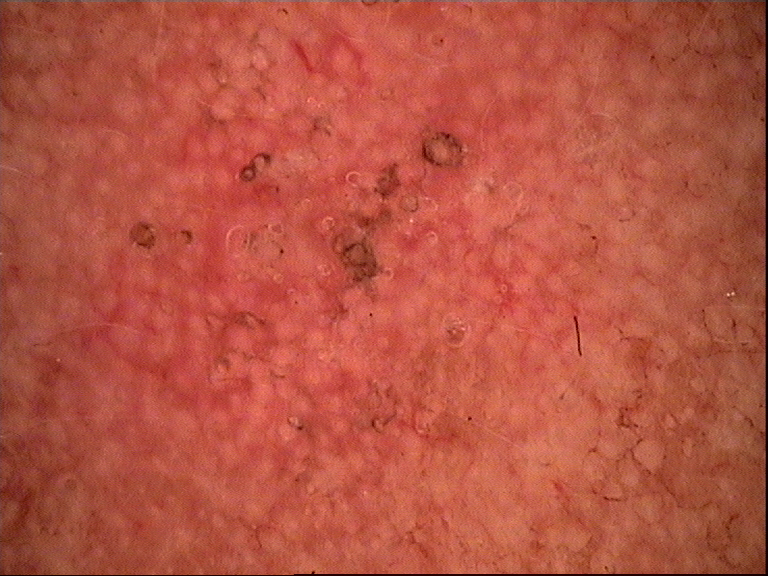Diagnosed as a keratinocytic lesion — an actinic keratosis.